The photo was captured at a distance; the contributor notes itching; the patient considered this a rash; the lesion is described as raised or bumpy; the patient is a male aged 18–29; the lesion involves the top or side of the foot — 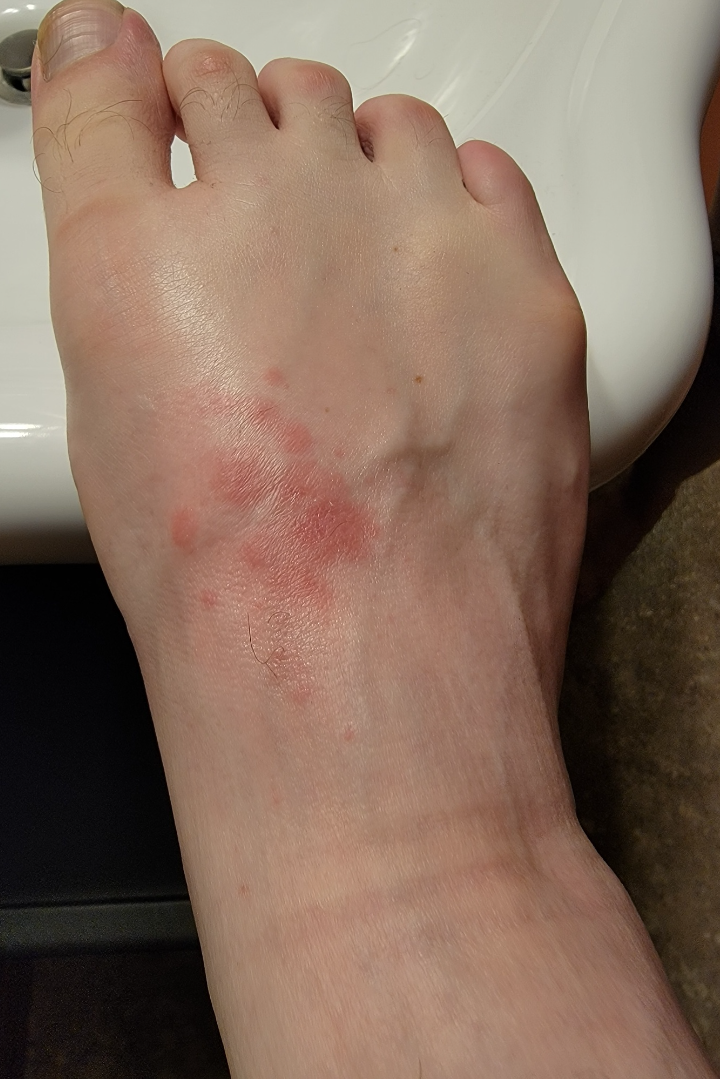Q: What is the dermatologist's impression?
A: the differential is split between Eczema, Allergic Contact Dermatitis and Irritant Contact Dermatitis